The arm is involved · the patient is 50–59, female · texture is reported as raised or bumpy · a close-up photograph · the condition has been present for three to twelve months · symptoms reported: enlargement: 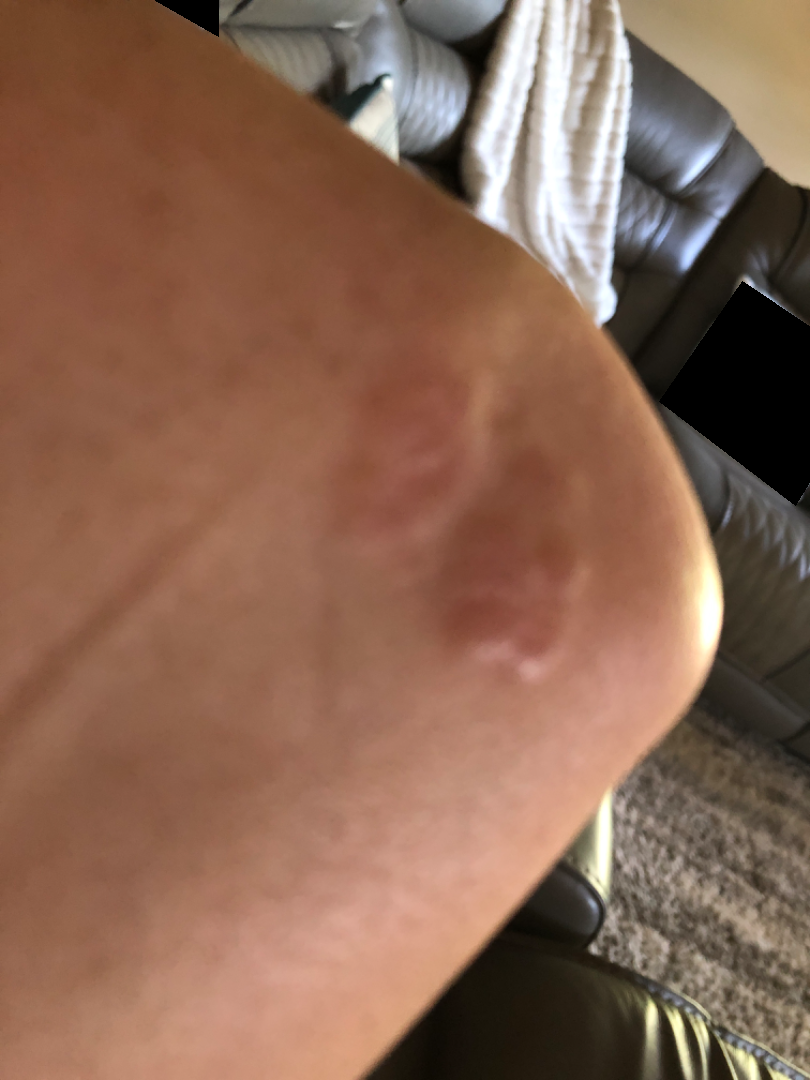| feature | finding |
|---|---|
| assessment | ungradable on photographic review |